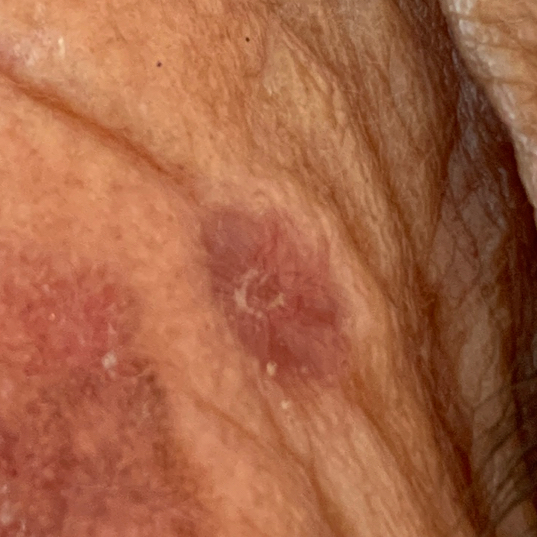image = smartphone clinical photo | patient = male, in their 70s | skin type = III | location = the face | diameter = 6x4 mm | pathology = basal cell carcinoma (biopsy-proven).